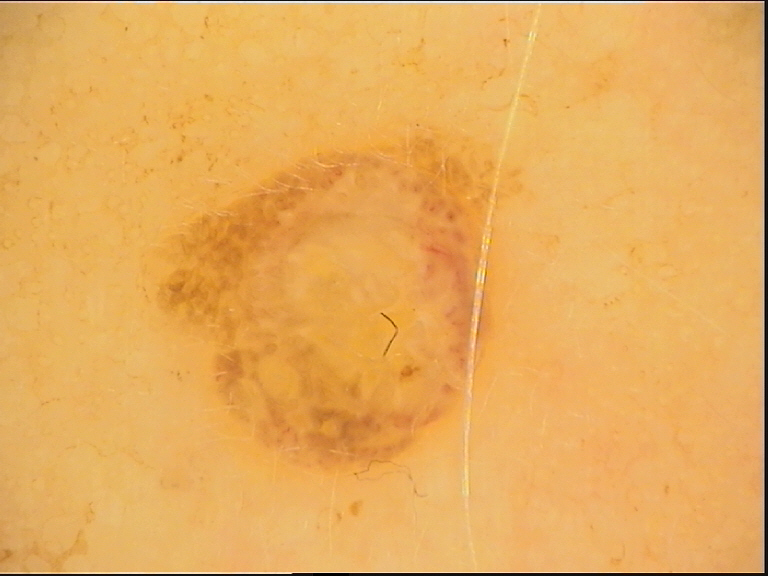Case: A dermoscopic image of a skin lesion. The morphology is that of a banal lesion. Conclusion: Labeled as a dermal nevus.